A clinical photo of a skin lesion taken with a smartphone · a male patient 62 years of age — 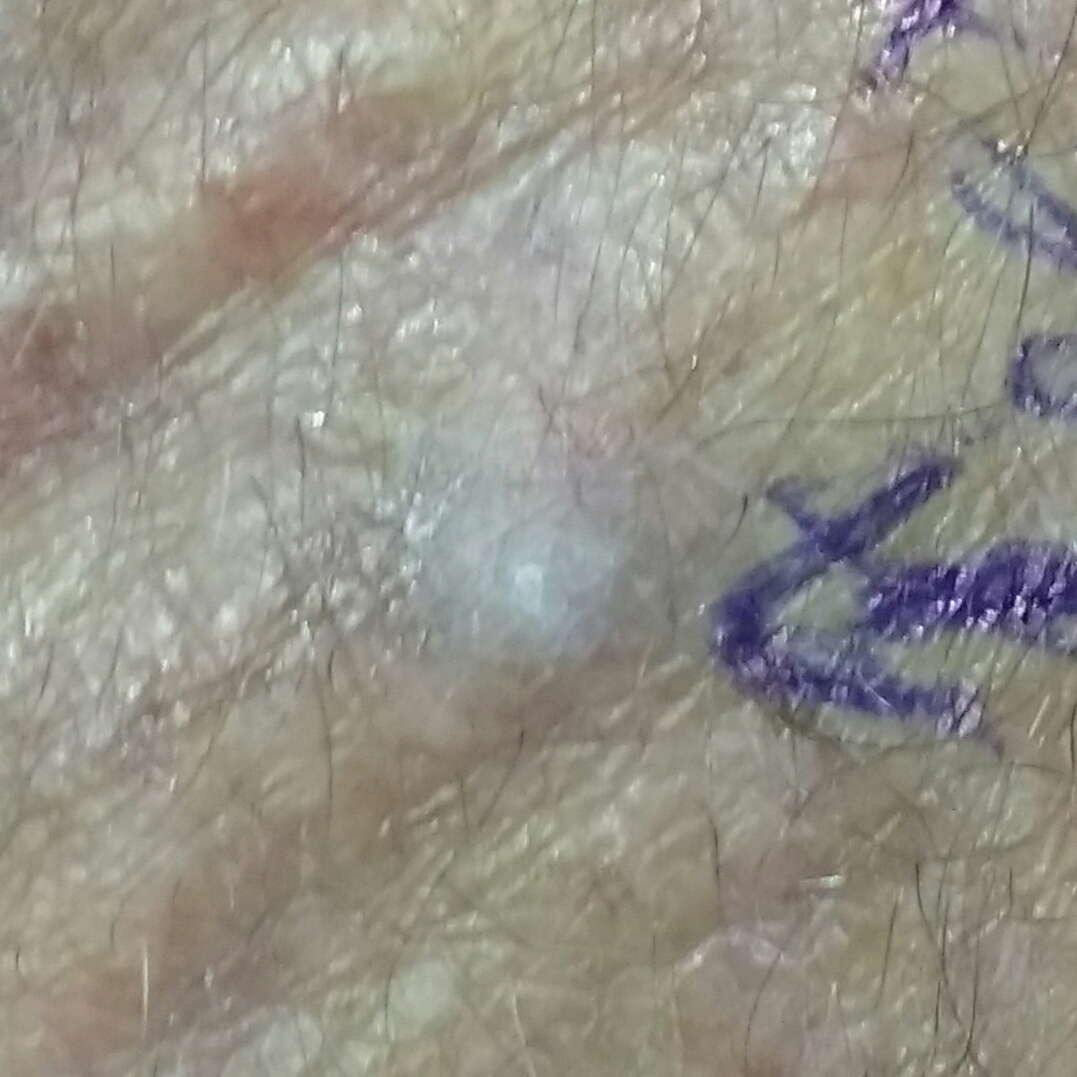Case summary: Located on a hand. The patient reports that the lesion hurts and is elevated. Conclusion: On biopsy, the diagnosis was a squamous cell carcinoma.